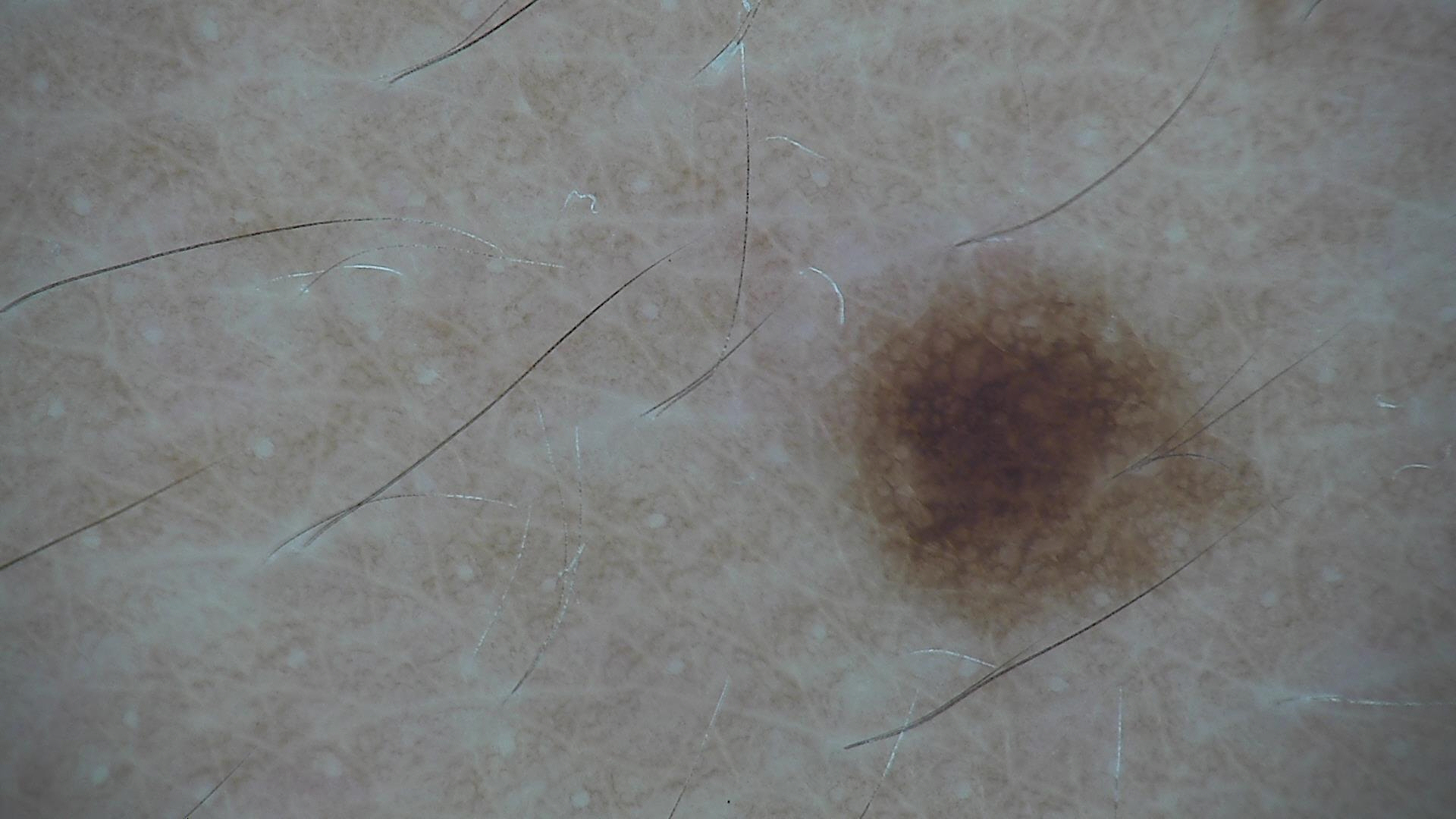– image: dermatoscopy
– diagnostic label: dysplastic junctional nevus (expert consensus)